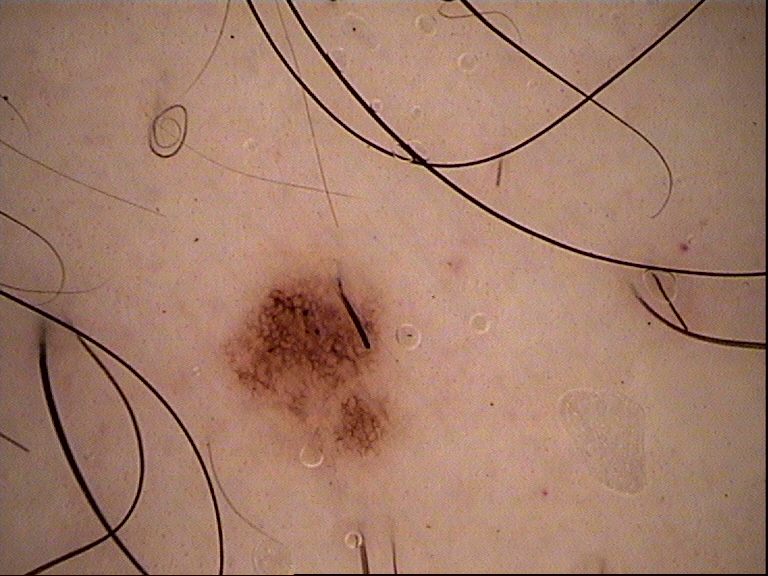Classified as a dysplastic junctional nevus.